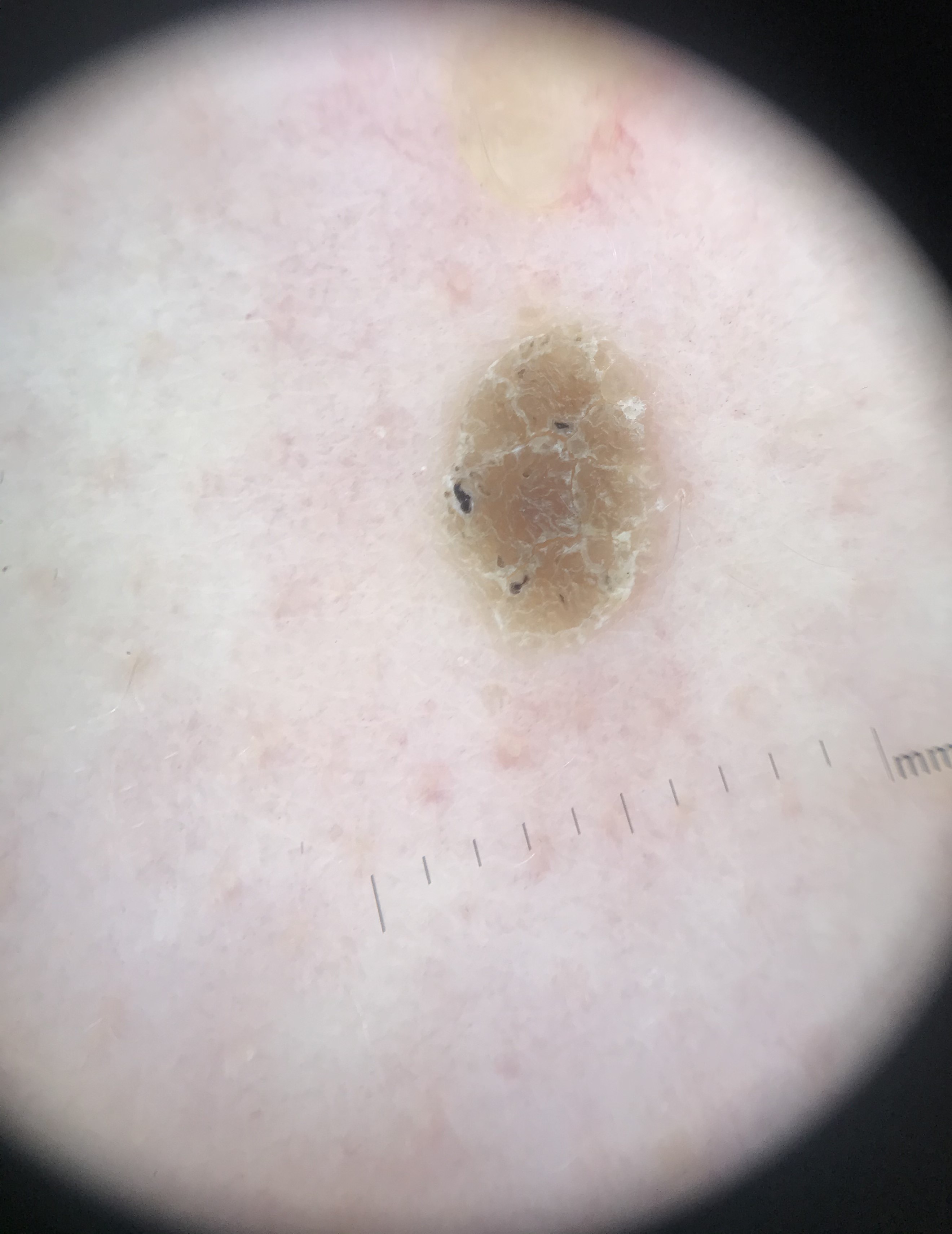The diagnosis was a seborrheic keratosis.